A clinical photograph showing a skin lesion in context. A female subject aged 73 to 77. The patient was assessed as FST II — 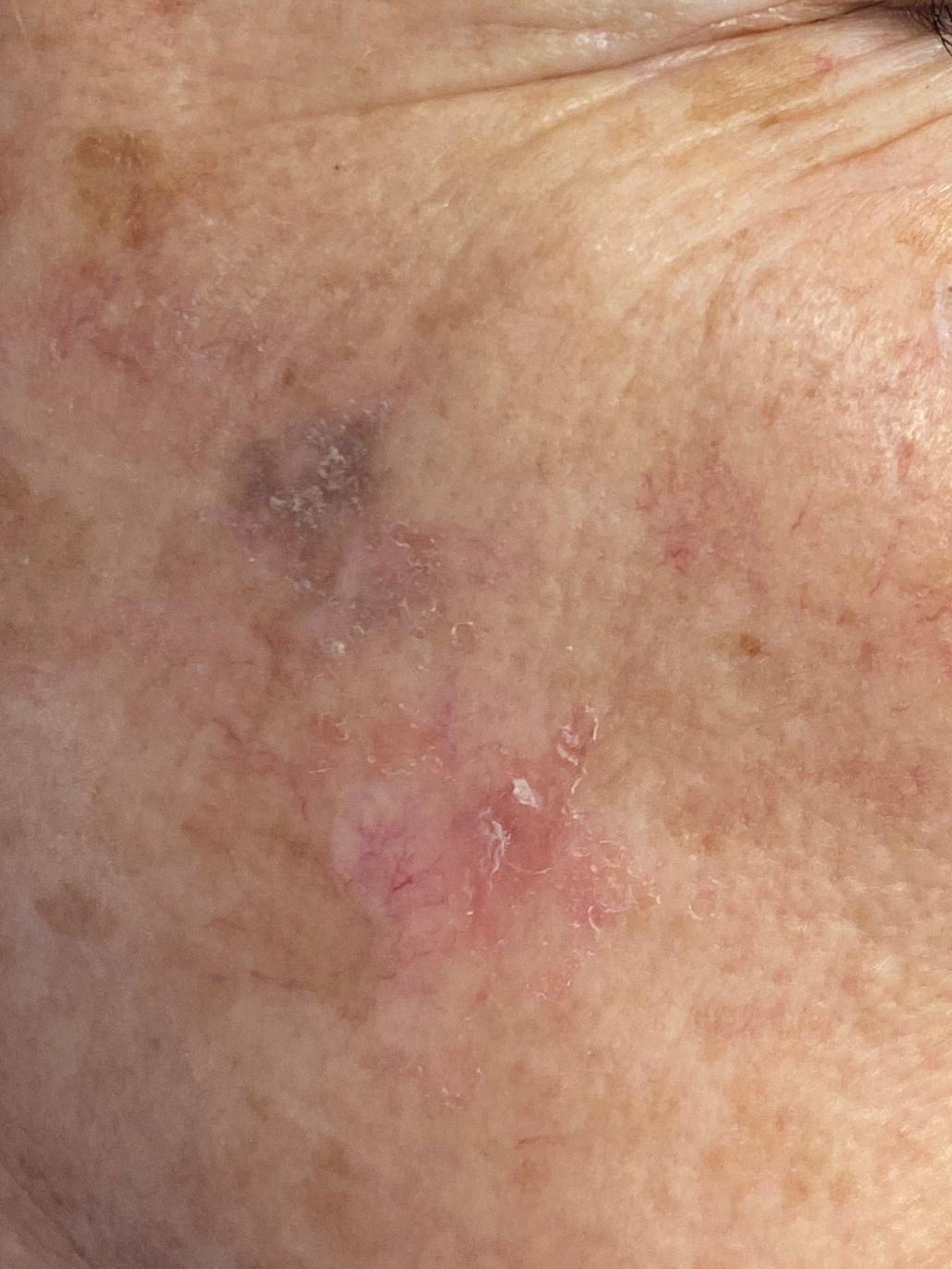– body site — the head or neck
– pathology — Squamous cell carcinoma (biopsy-proven)